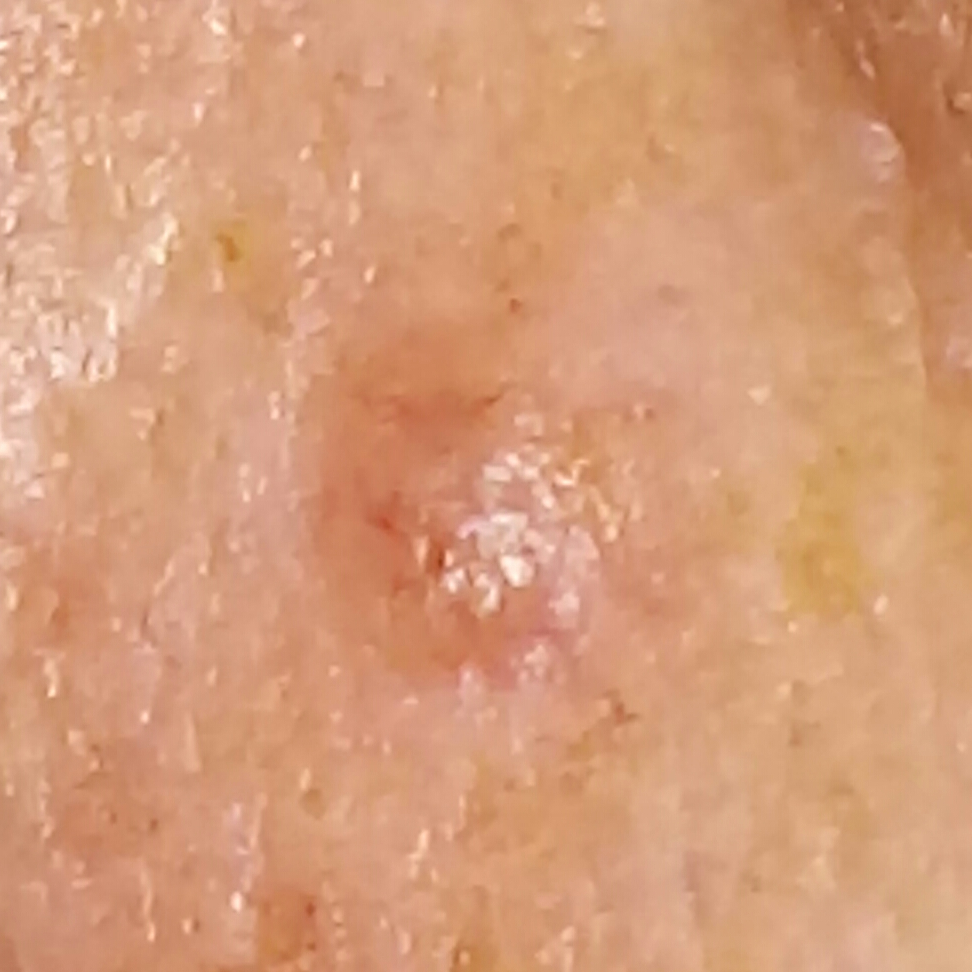| field | value |
|---|---|
| subject | female, in their 50s |
| risk factors | prior skin cancer (patient or family), prior malignancy (patient or family), pesticide exposure |
| skin type | III |
| image type | smartphone clinical photo |
| anatomic site | the face |
| lesion diameter | approx. 5 × 4 mm |
| reported symptoms | itching, elevation |
| diagnostic label | basal cell carcinoma (biopsy-proven) |